The contributor reports the condition has been present for about one day · an image taken at a distance · the affected area is the palm, leg, head or neck, sole of the foot and arm · the patient is a female aged 18–29 · symptoms reported: burning and itching · texture is reported as raised or bumpy.
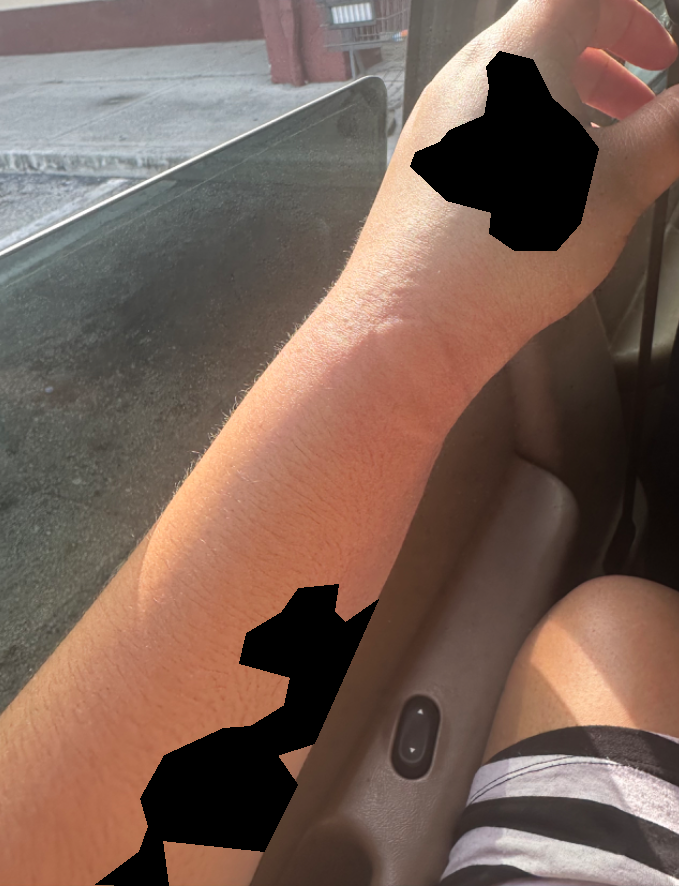clinical impression=one reviewing dermatologist: most likely Urticaria; also consider Drug Rash.